A skin lesion imaged with a dermatoscope — 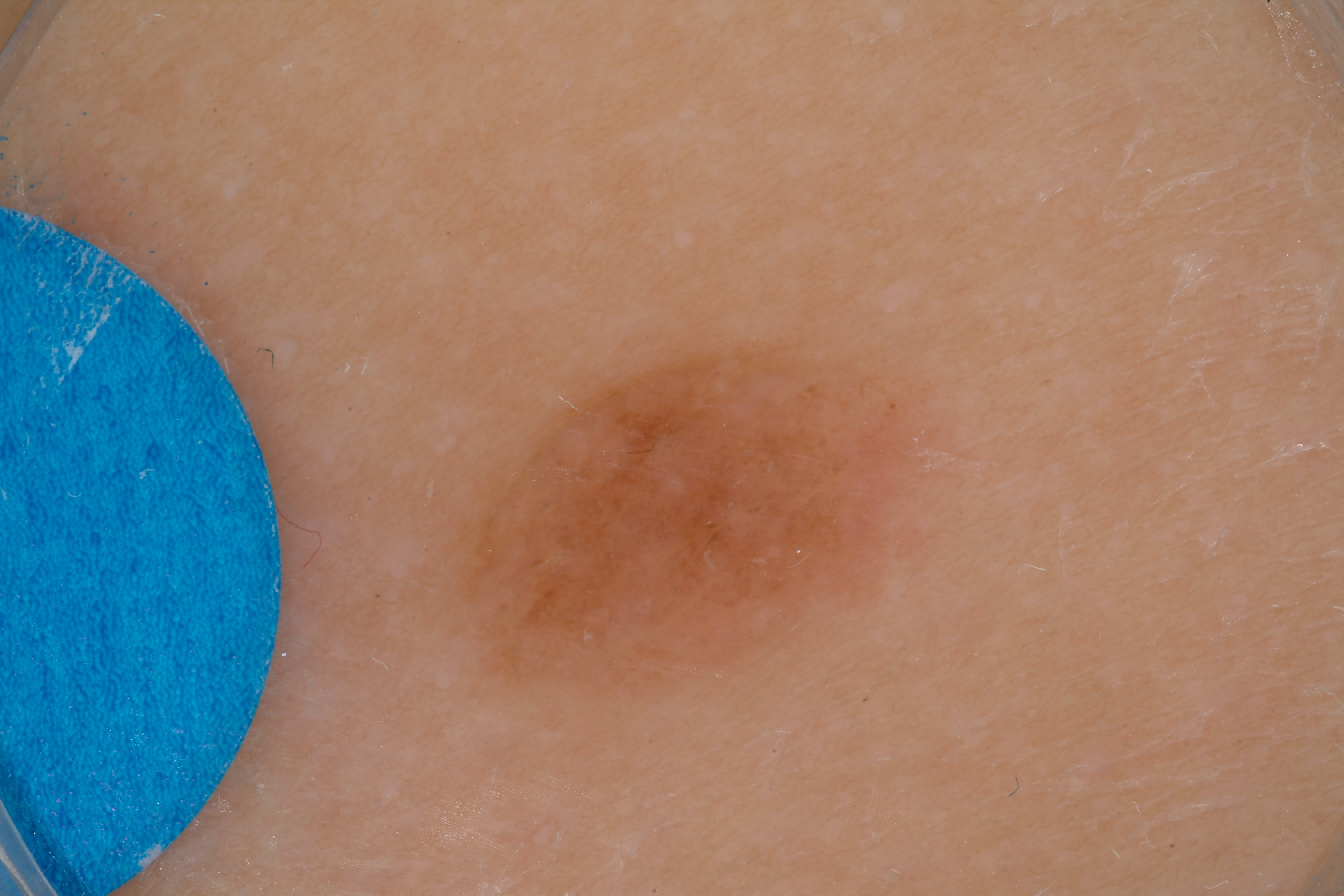{"lesion_location": {"bbox_xyxy": [463, 346, 929, 689]}, "diagnosis": {"name": "melanocytic nevus", "malignancy": "benign", "lineage": "melanocytic", "provenance": "clinical"}}